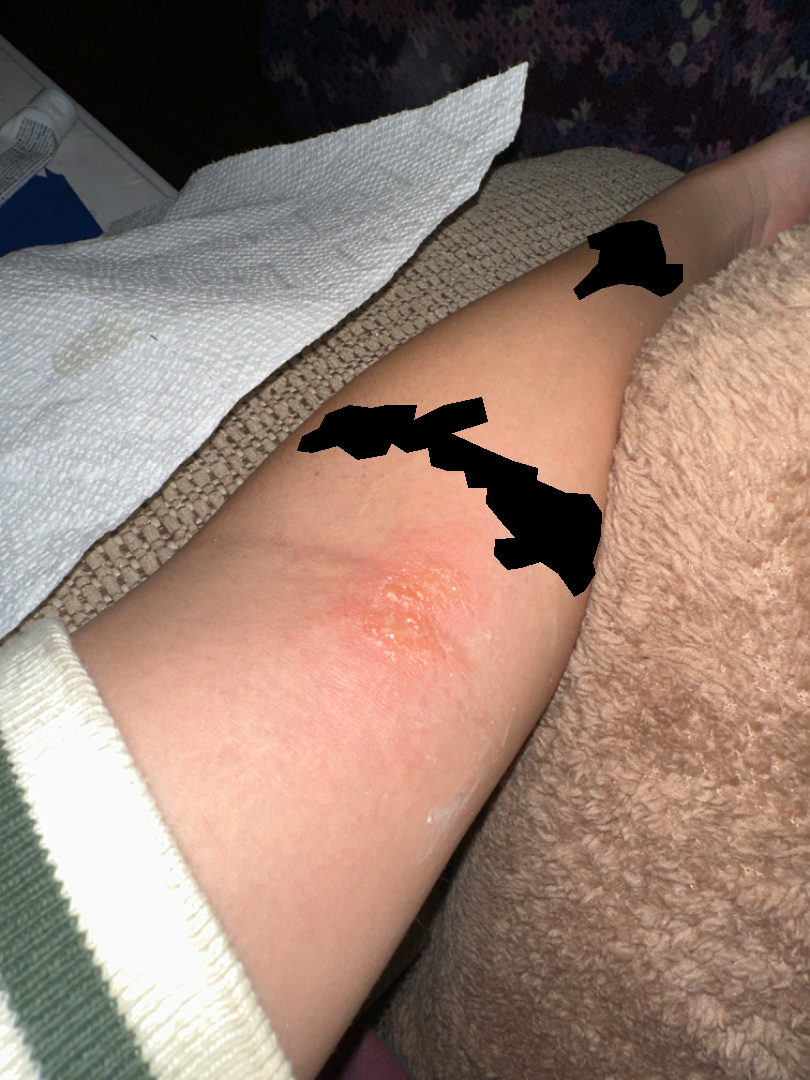diagnostic considerations — Eczema (primary); Allergic Contact Dermatitis (considered).